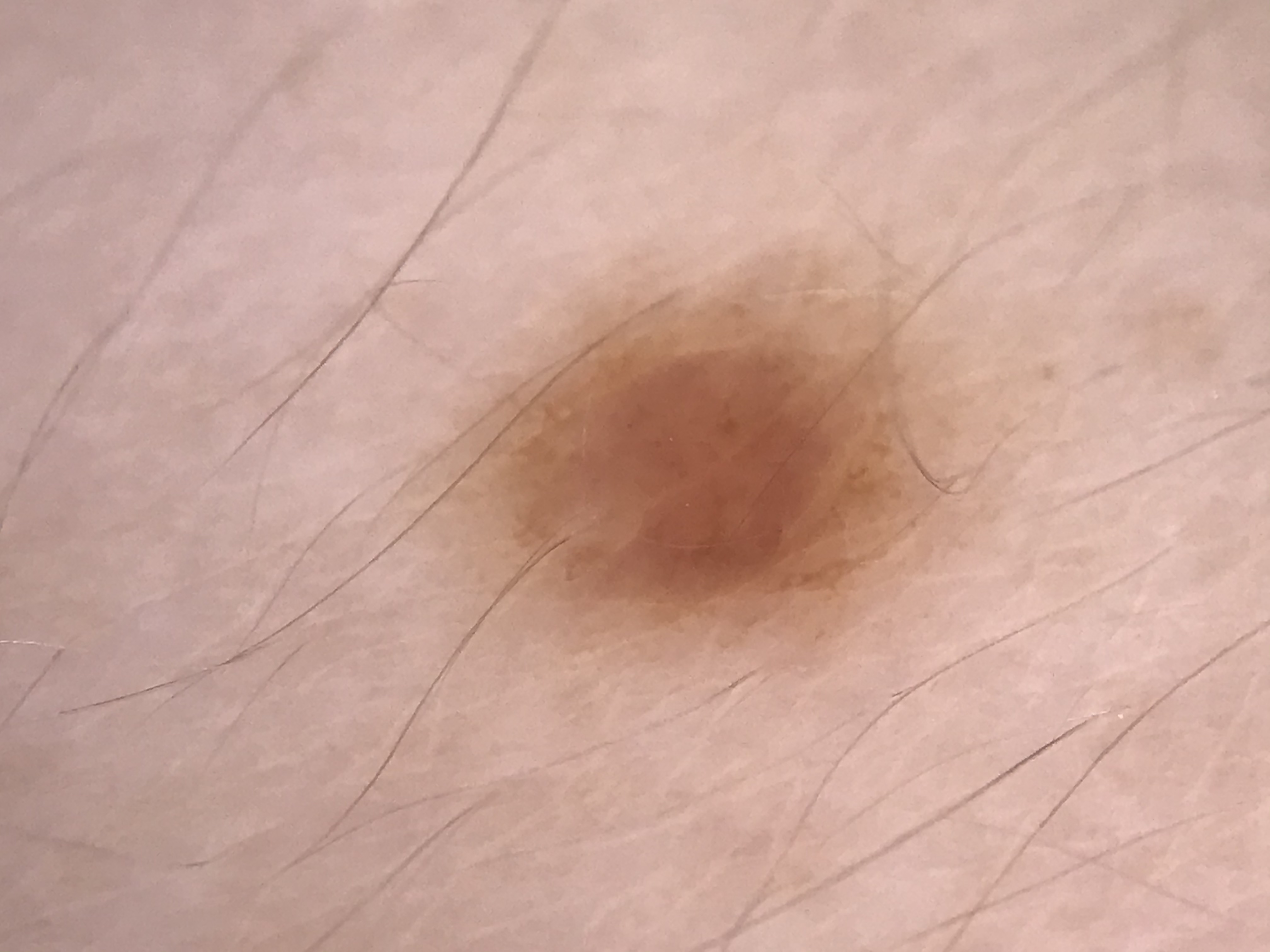– label: compound nevus (expert consensus)